The photo was captured at a distance:
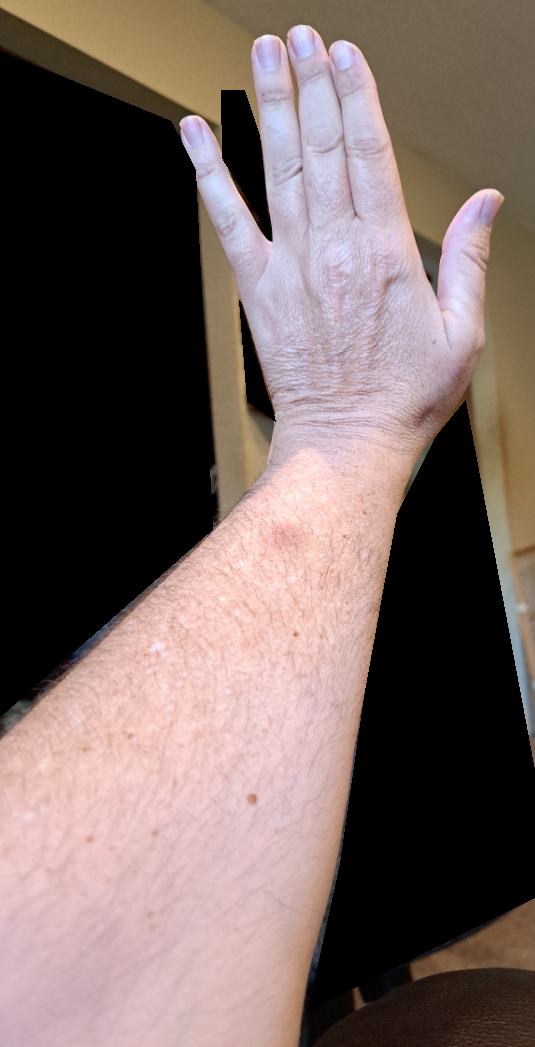assessment: indeterminate from the photograph.